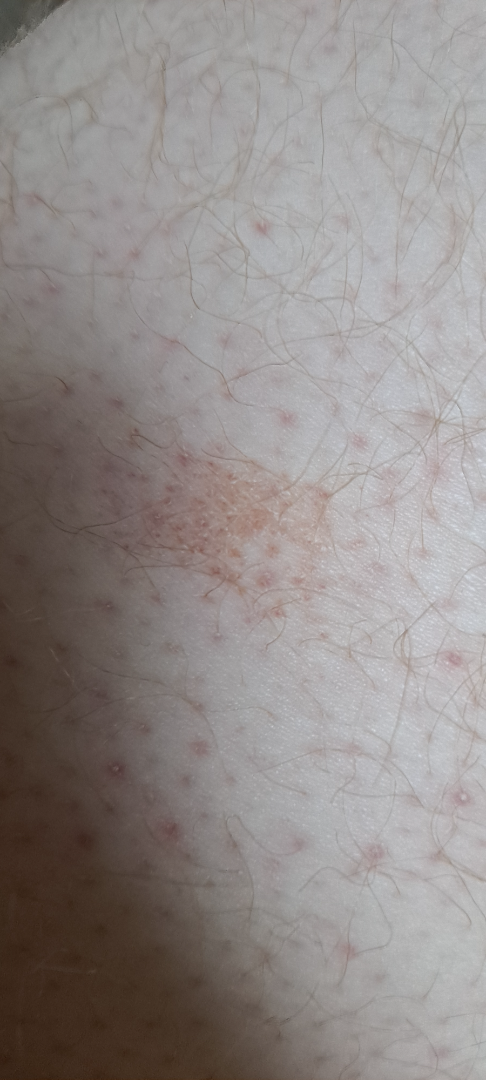– assessment · not assessable
– shot type · close-up
– skin tone · FST II